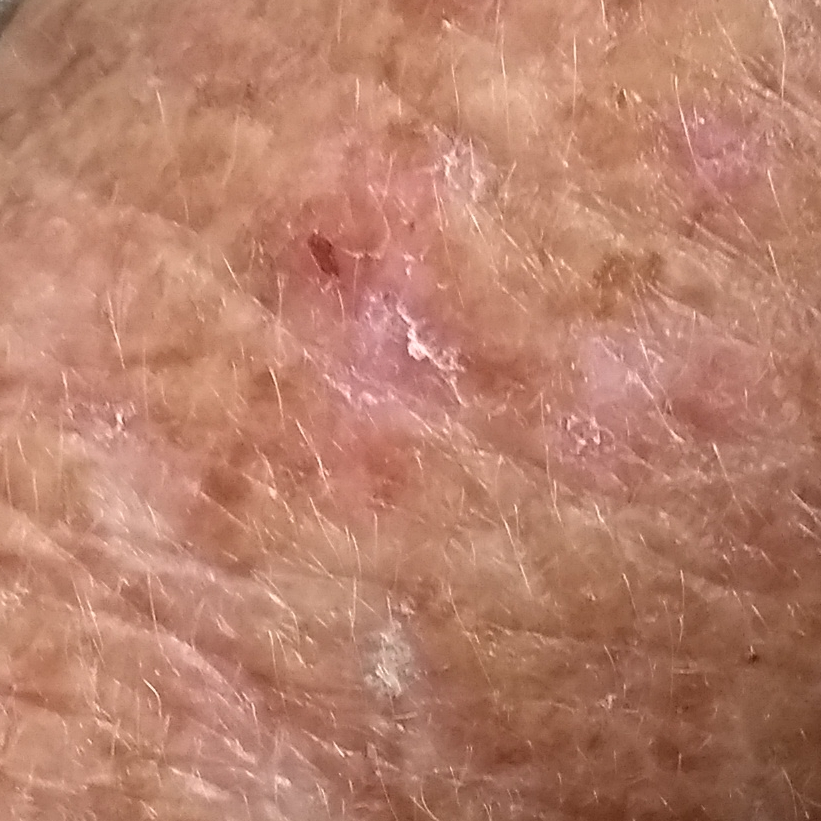A clinical photo of a skin lesion taken with a smartphone. The lesion is located on a forearm. The patient describes that the lesion has grown and itches, but does not hurt and has not changed. The clinical impression was a premalignant lesion — an actinic keratosis.